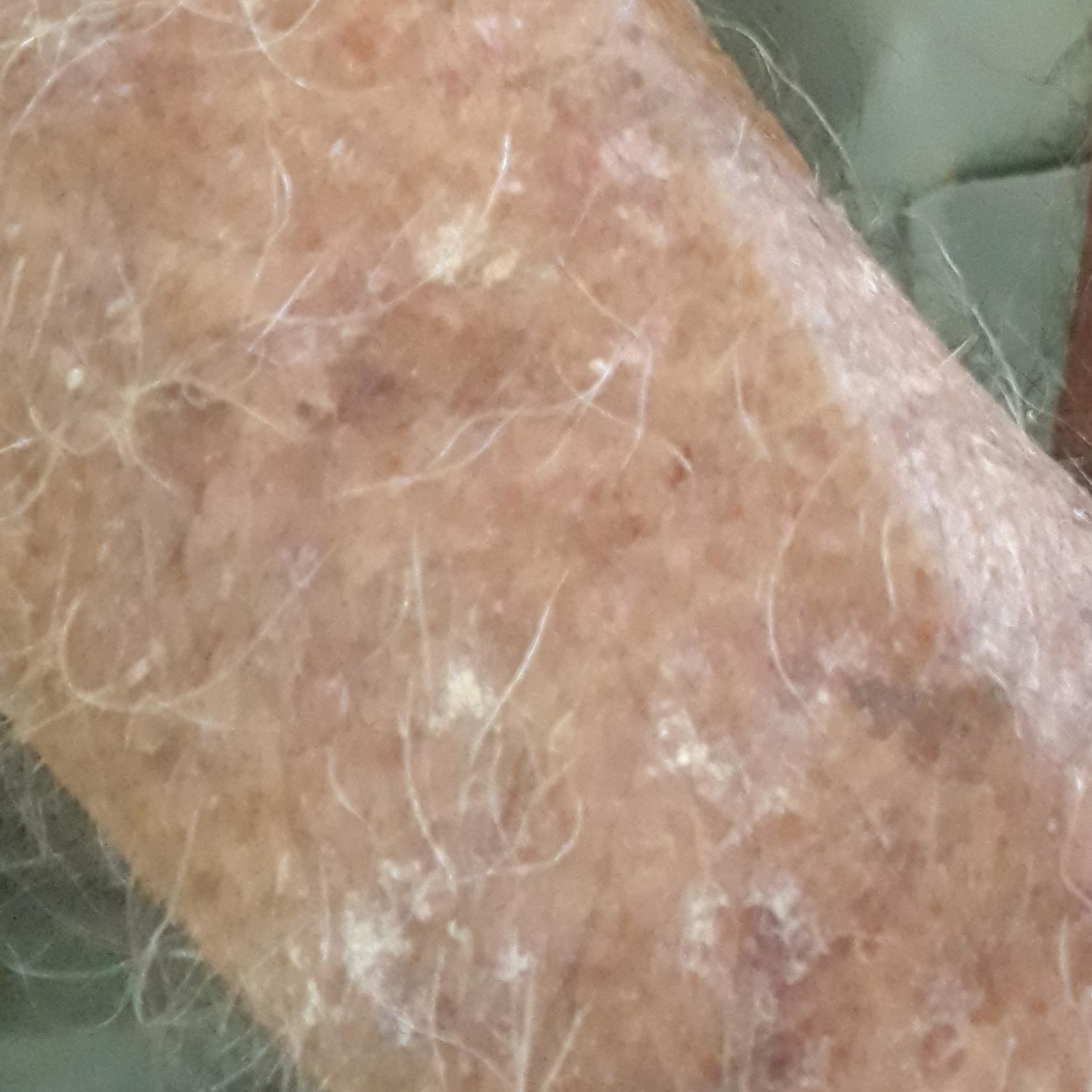A clinical photo of a skin lesion taken with a smartphone. A patient aged 81. The lesion was found on a forearm. Per patient report, the lesion itches. Diagnosed by dermatologist consensus as a premalignant lesion — an actinic keratosis.